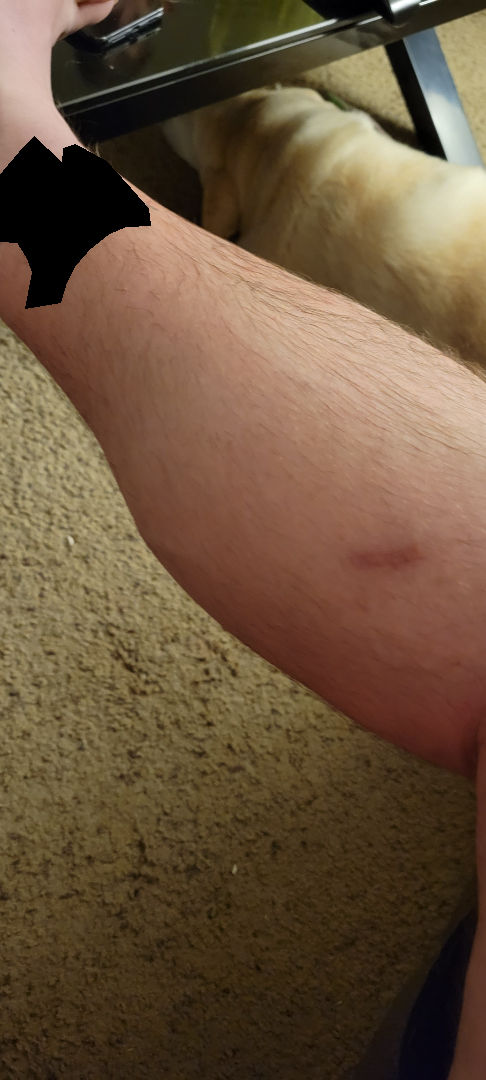• assessment · indeterminate from the photograph